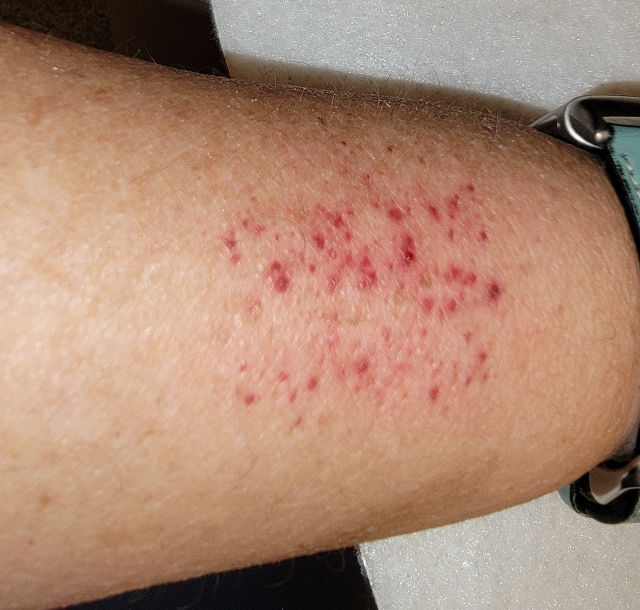The differential, in no particular order, includes Contact purpura and Purpura; less likely is Vasculitis of the skin, NOS.